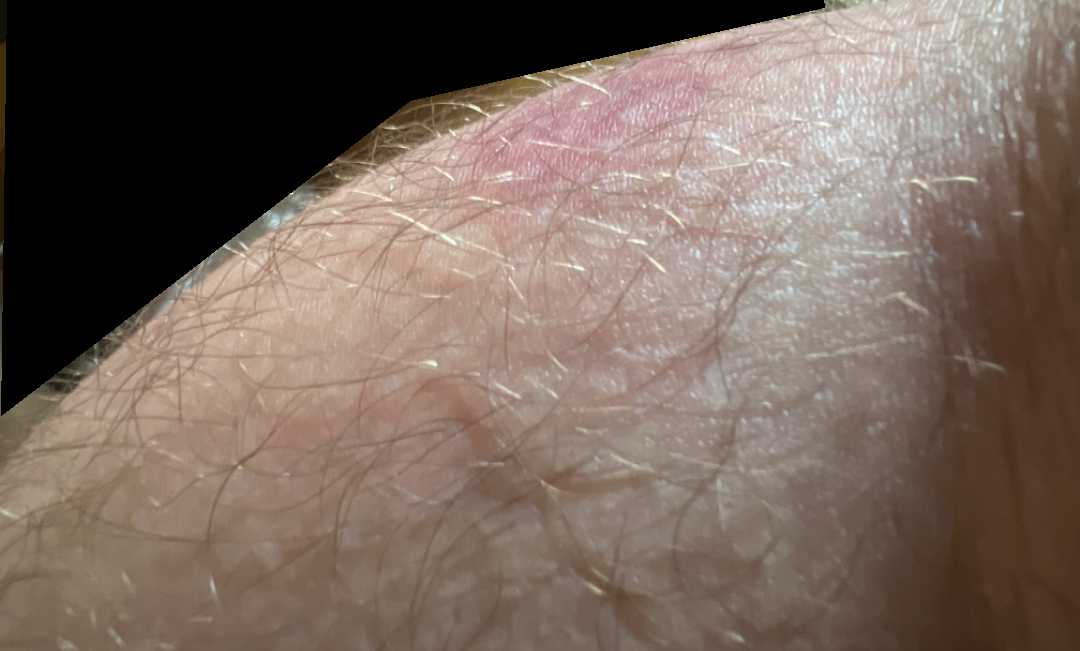This image was taken at an angle. The patient notes the lesion is fluid-filled and raised or bumpy. Most likely Eczema.